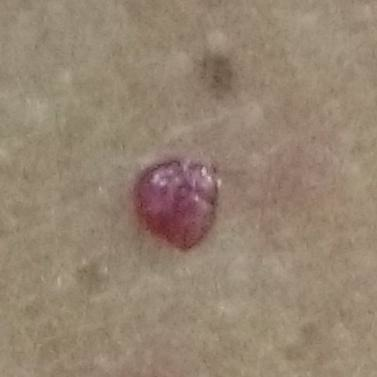A clinical close-up photograph of a skin lesion.
A patient 48 years old.
The consensus clinical diagnosis was a benign lesion — a nevus.